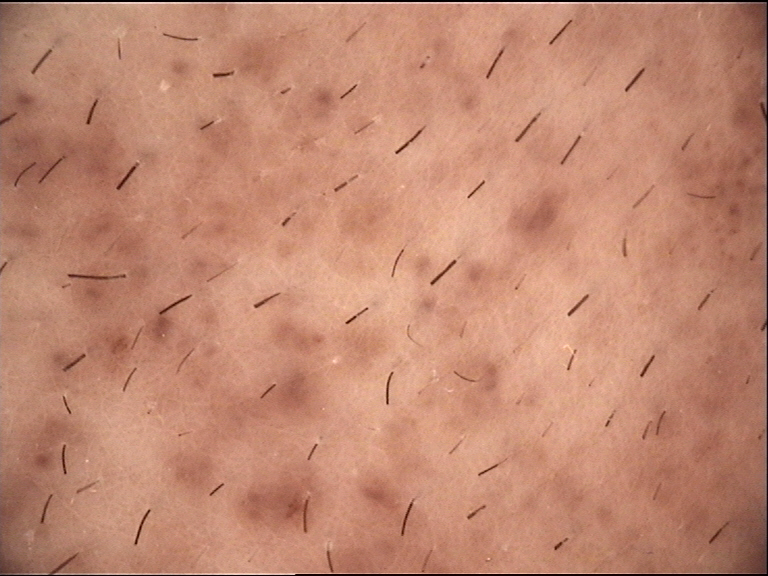The diagnostic label was a banal lesion — a congenital compound nevus.